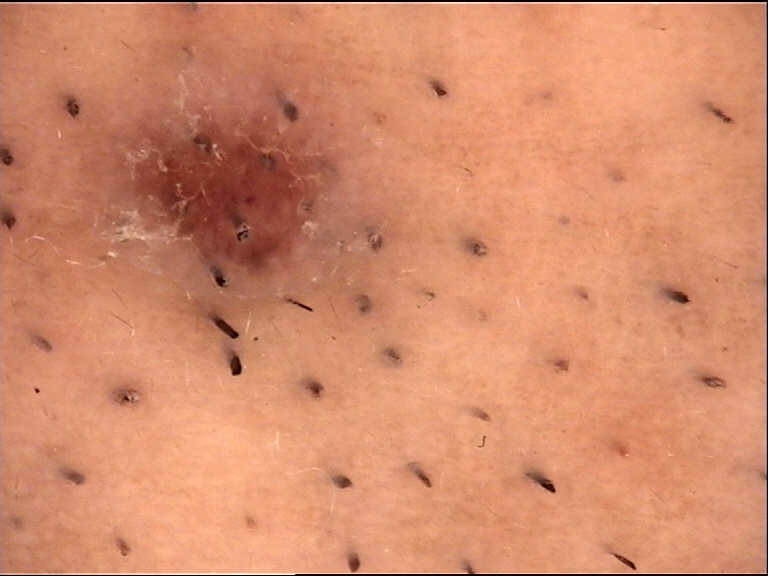A dermoscopic photograph of a skin lesion. This is a compound, banal lesion. Diagnosed as a Miescher nevus.